A dermoscopy image of a single skin lesion:
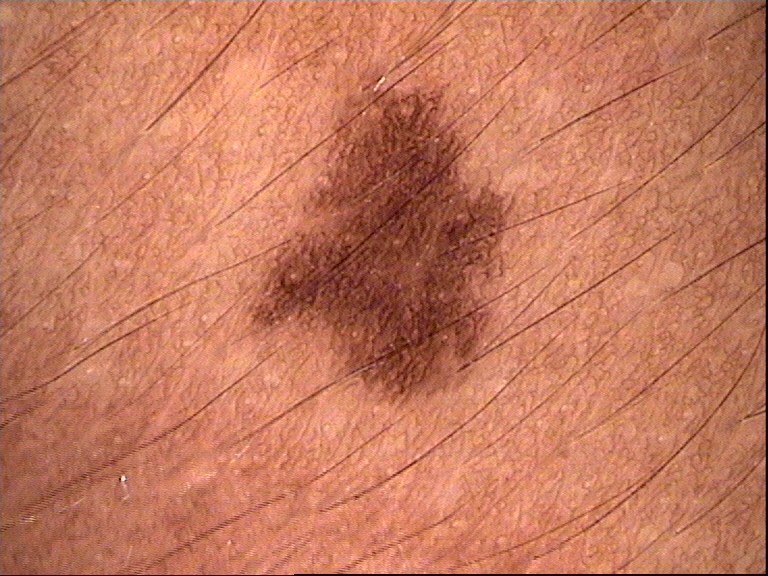diagnostic label — dysplastic junctional nevus (expert consensus)